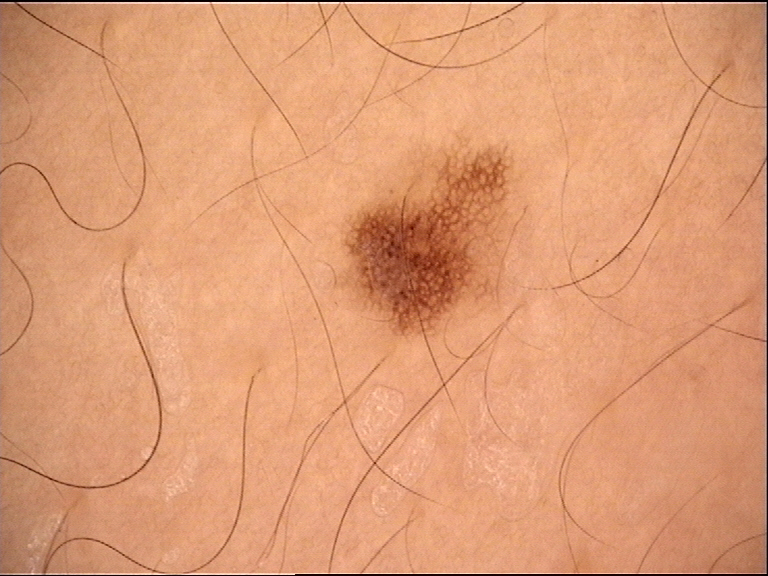| key | value |
|---|---|
| diagnostic label | dysplastic junctional nevus (expert consensus) |